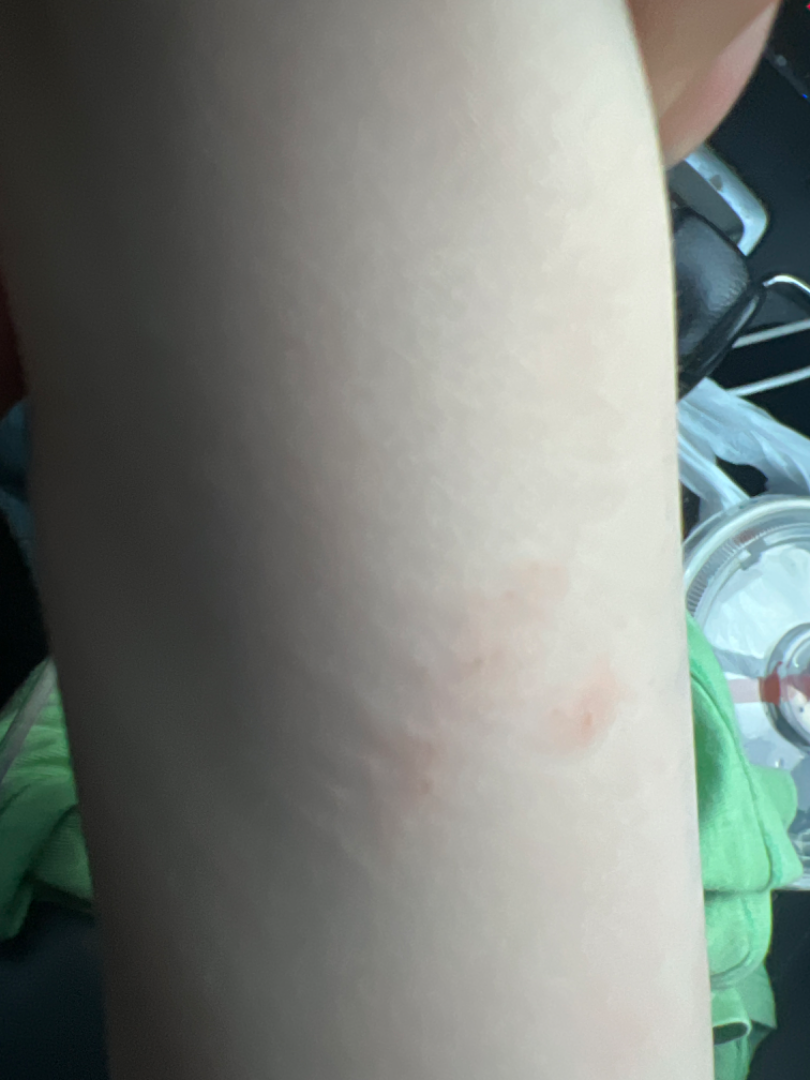No differential diagnosis could be assigned on photographic review.